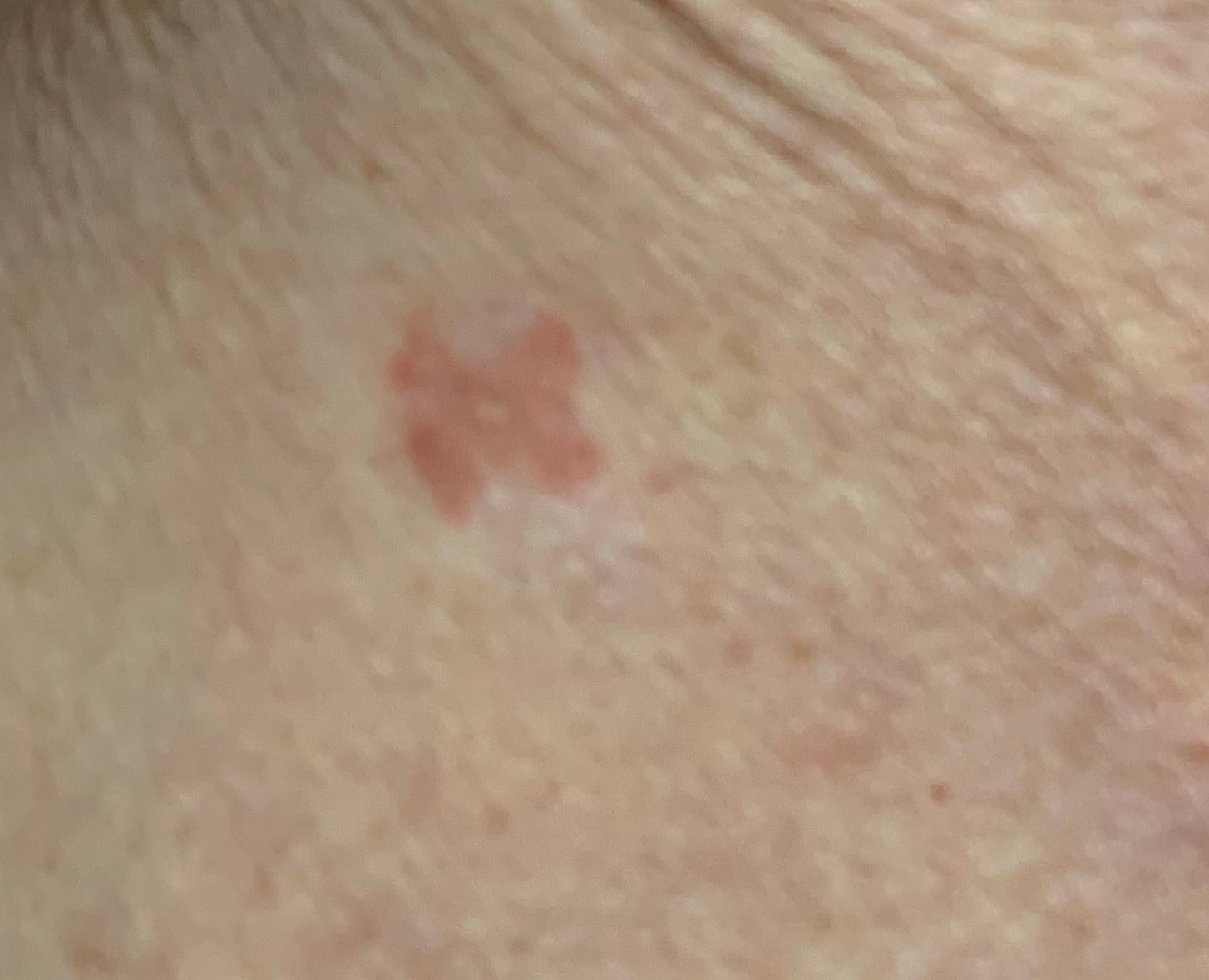Clinical context: A clinical photograph of a skin lesion. The patient is Fitzpatrick II. A male subject approximately 65 years of age. The lesion is located on the trunk. Conclusion: The biopsy diagnosis was a lesion of epidermal origin — a squamous cell carcinoma.